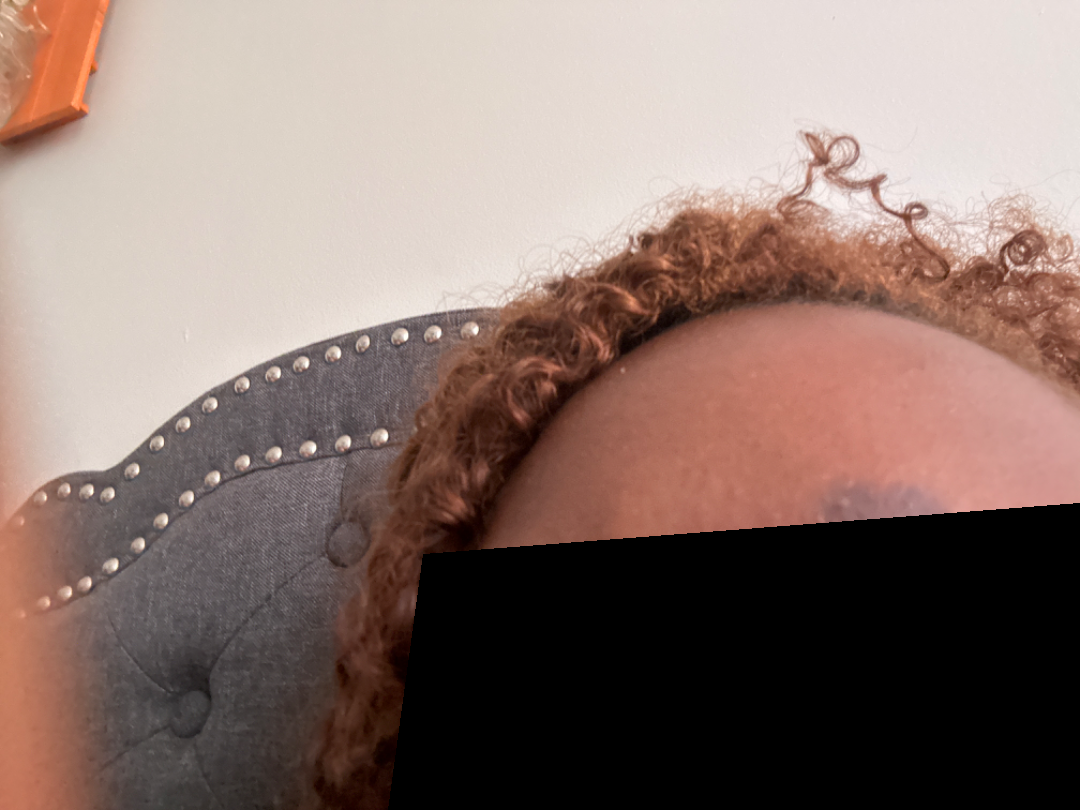{
  "duration": "three to twelve months",
  "patient_category": "a pigmentary problem",
  "skin_tone": {
    "fitzpatrick": "V",
    "monk_skin_tone": [
      5,
      7
    ]
  },
  "patient": "female, age 18–29",
  "texture": [
    "rough or flaky",
    "flat"
  ],
  "shot_type": "at an angle",
  "symptoms": [
    "darkening",
    "bothersome appearance"
  ],
  "differential": [
    "Traction alopecia",
    "Frontal fibrosing alopecia"
  ]
}